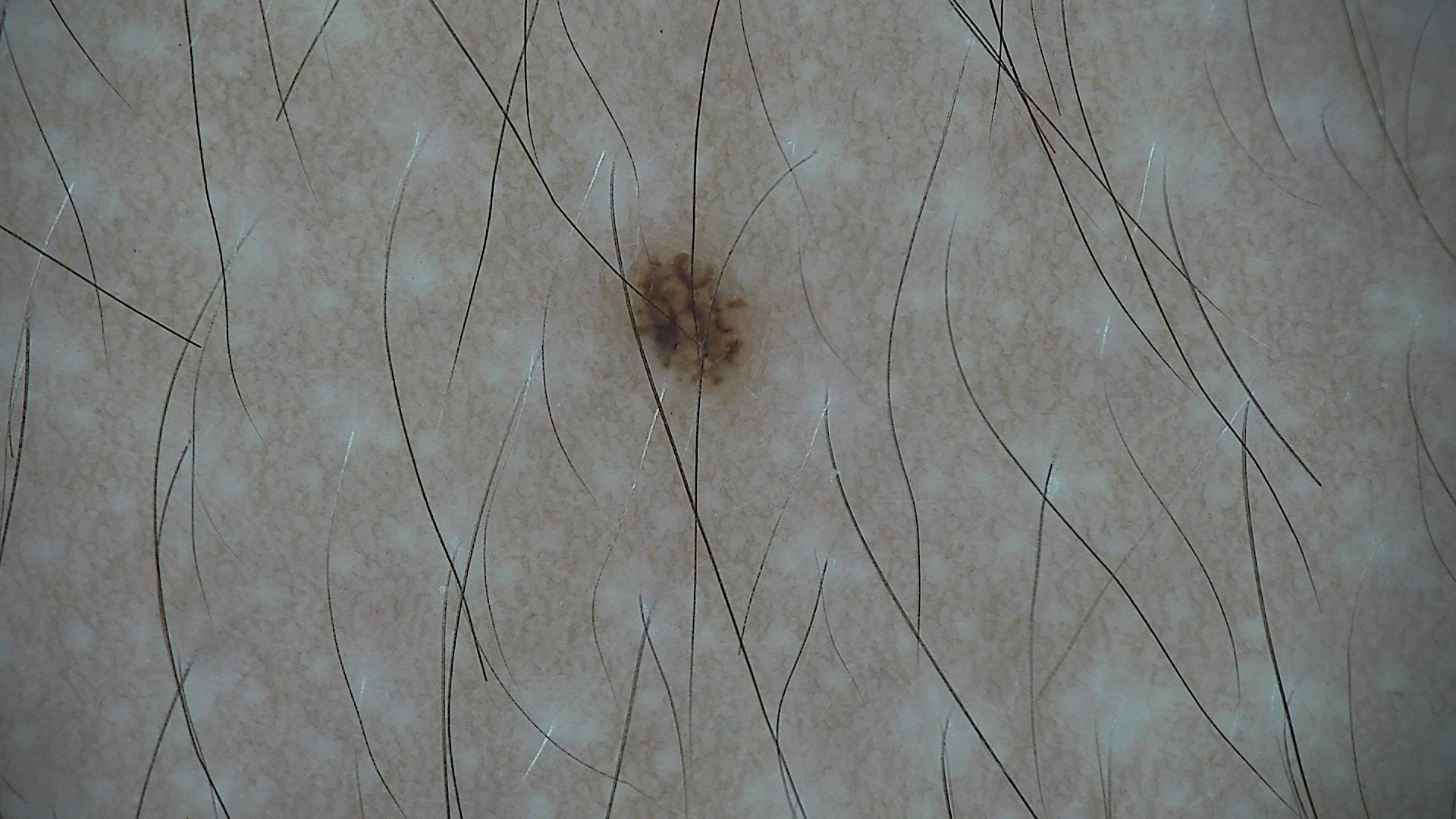| feature | finding |
|---|---|
| imaging | dermatoscopy |
| class | dysplastic junctional nevus (expert consensus) |